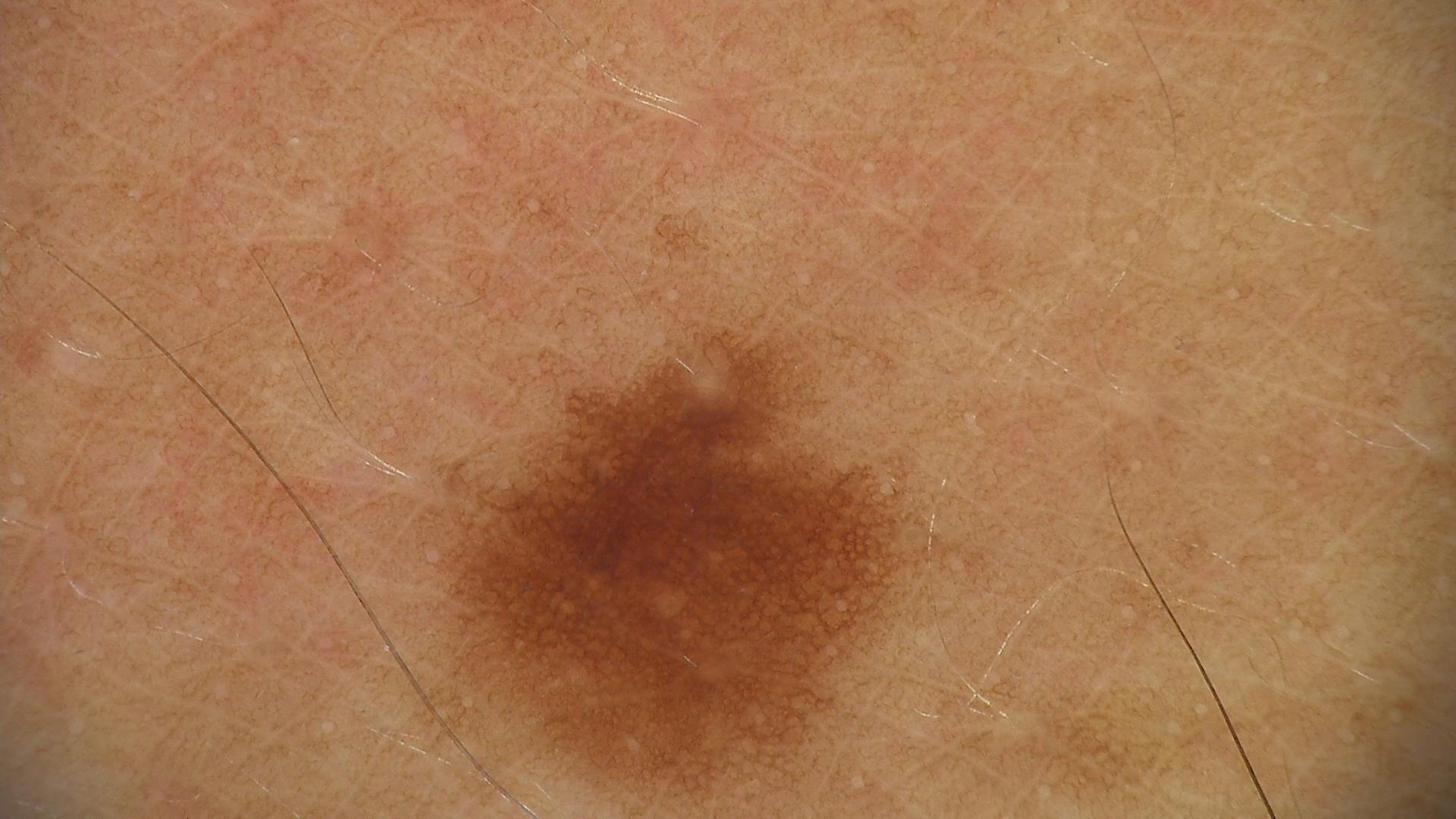Q: What is the diagnosis?
A: dysplastic junctional nevus (expert consensus)